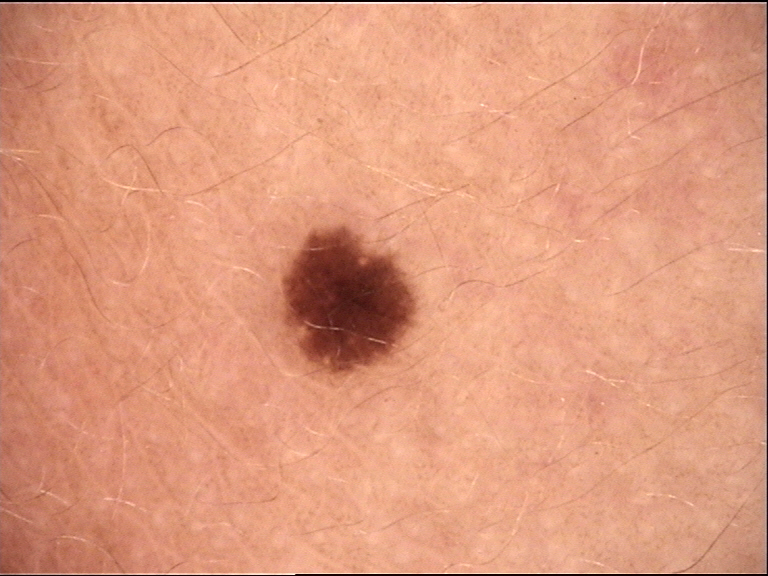A dermoscopy image of a single skin lesion. The architecture is that of a banal lesion. The diagnostic label was a junctional nevus.